A skin lesion imaged with a dermatoscope:
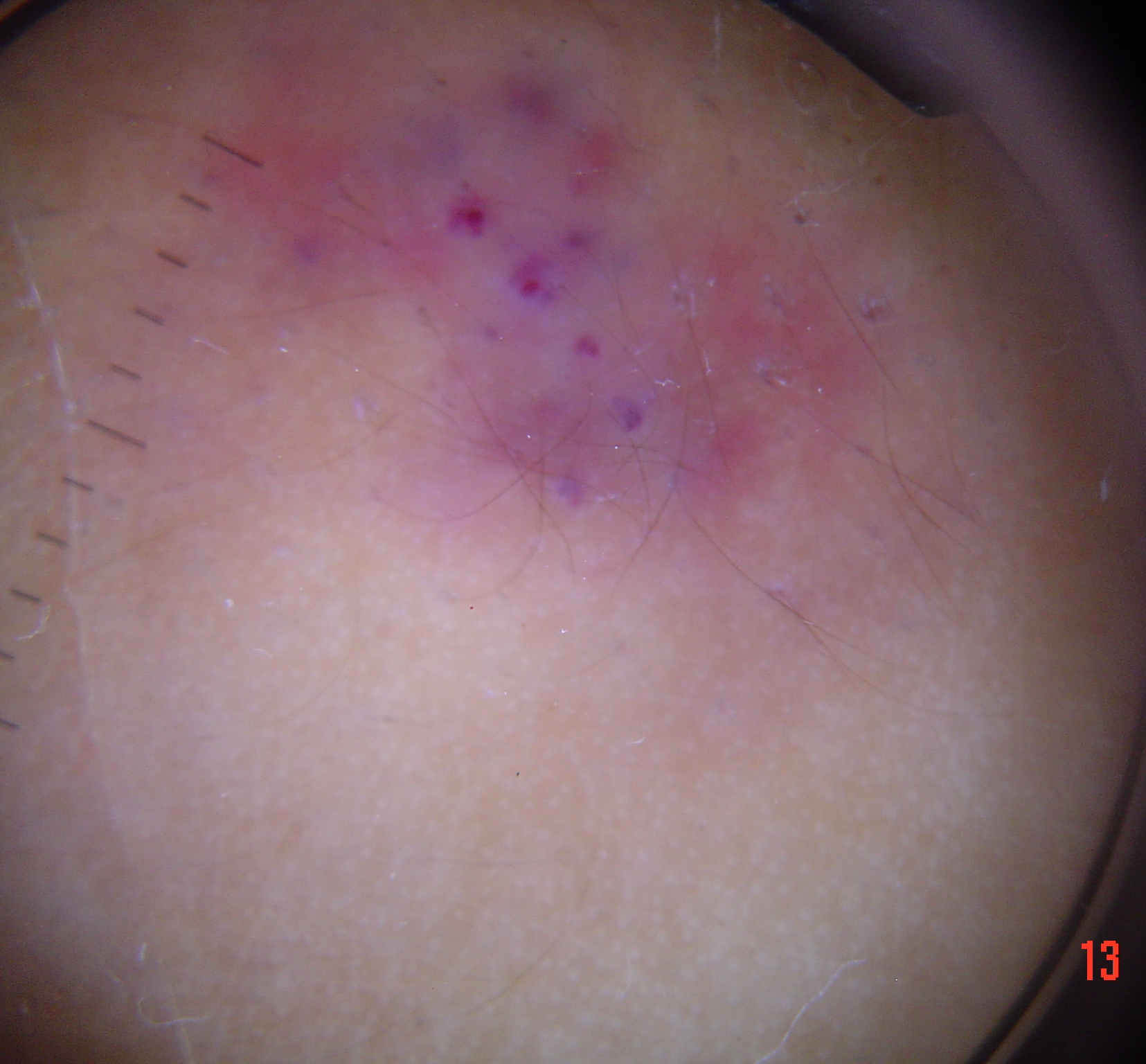subtype — vascular | diagnosis — angiokeratoma (expert consensus).